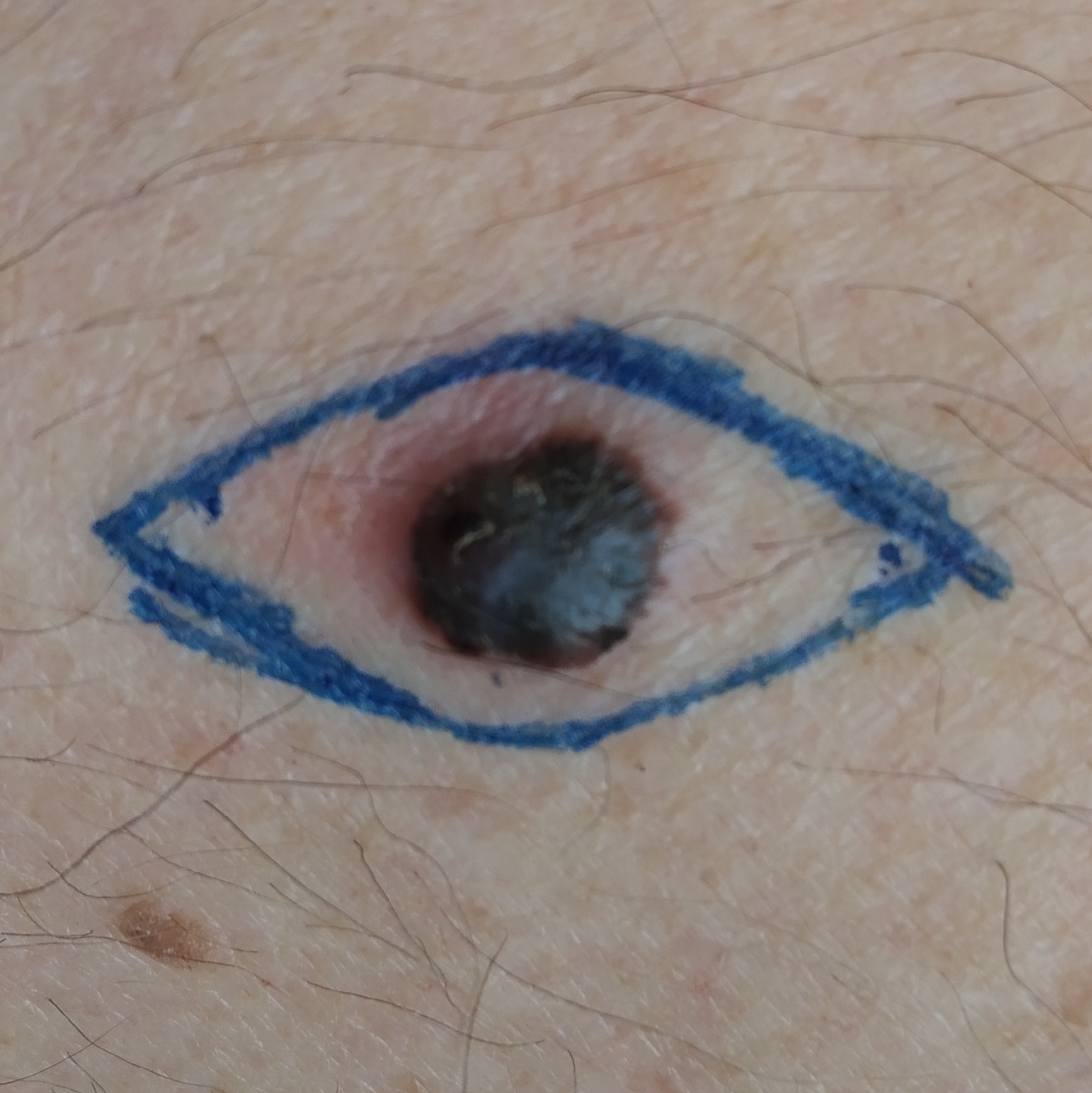The patient was assessed as Fitzpatrick II. A clinical close-up photograph of a skin lesion. The chart records prior malignancy (patient or family). The lesion is on an arm. Measuring about 10 × 9 mm. The patient describes that the lesion is elevated. The biopsy diagnosis was a malignant skin lesion — a melanoma.